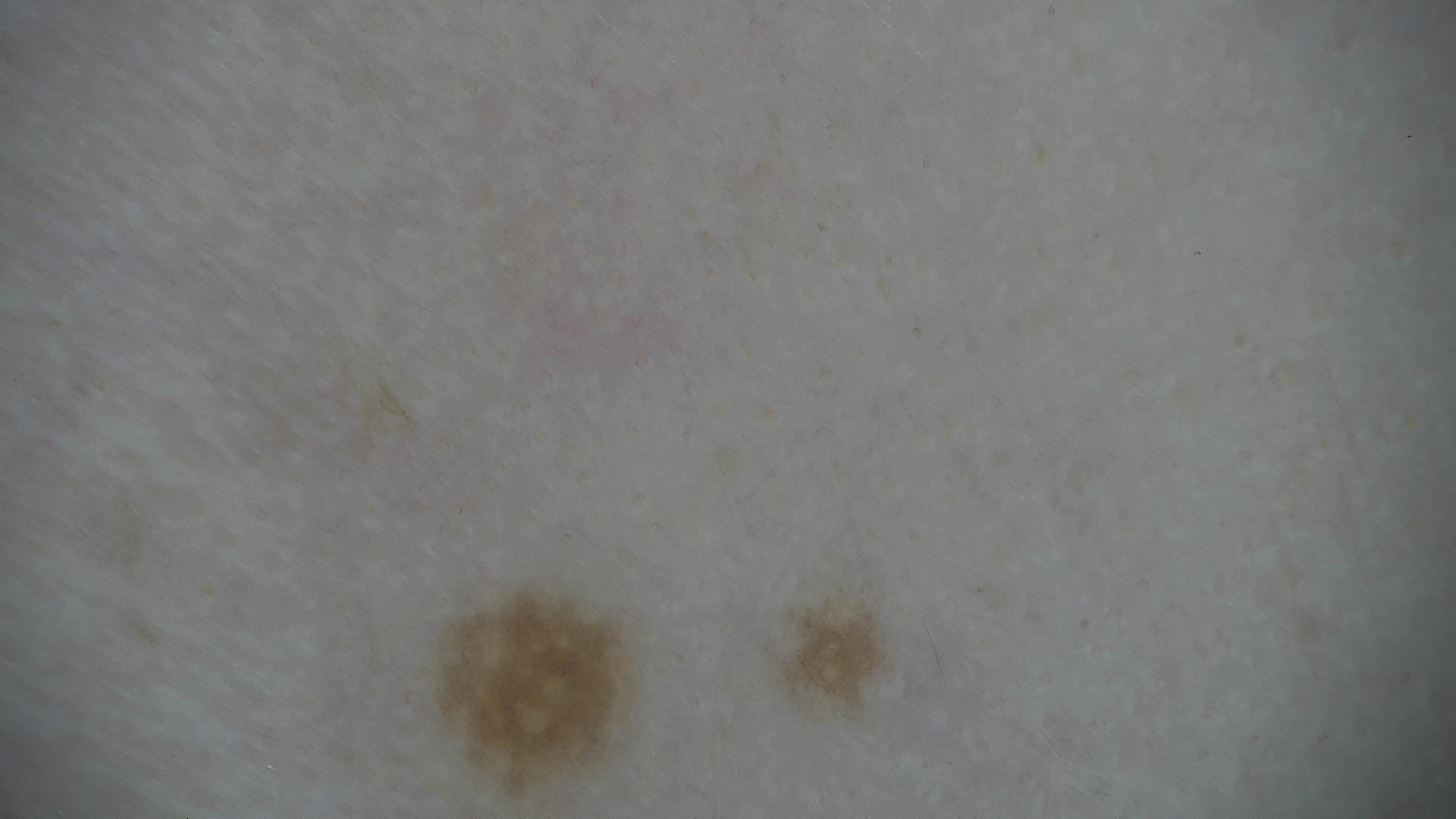<dermoscopy>
  <diagnosis>
    <name>Miescher nevus</name>
    <code>mcb</code>
    <malignancy>benign</malignancy>
    <super_class>melanocytic</super_class>
    <confirmation>expert consensus</confirmation>
  </diagnosis>
</dermoscopy>